A dermoscopy image of a single skin lesion:
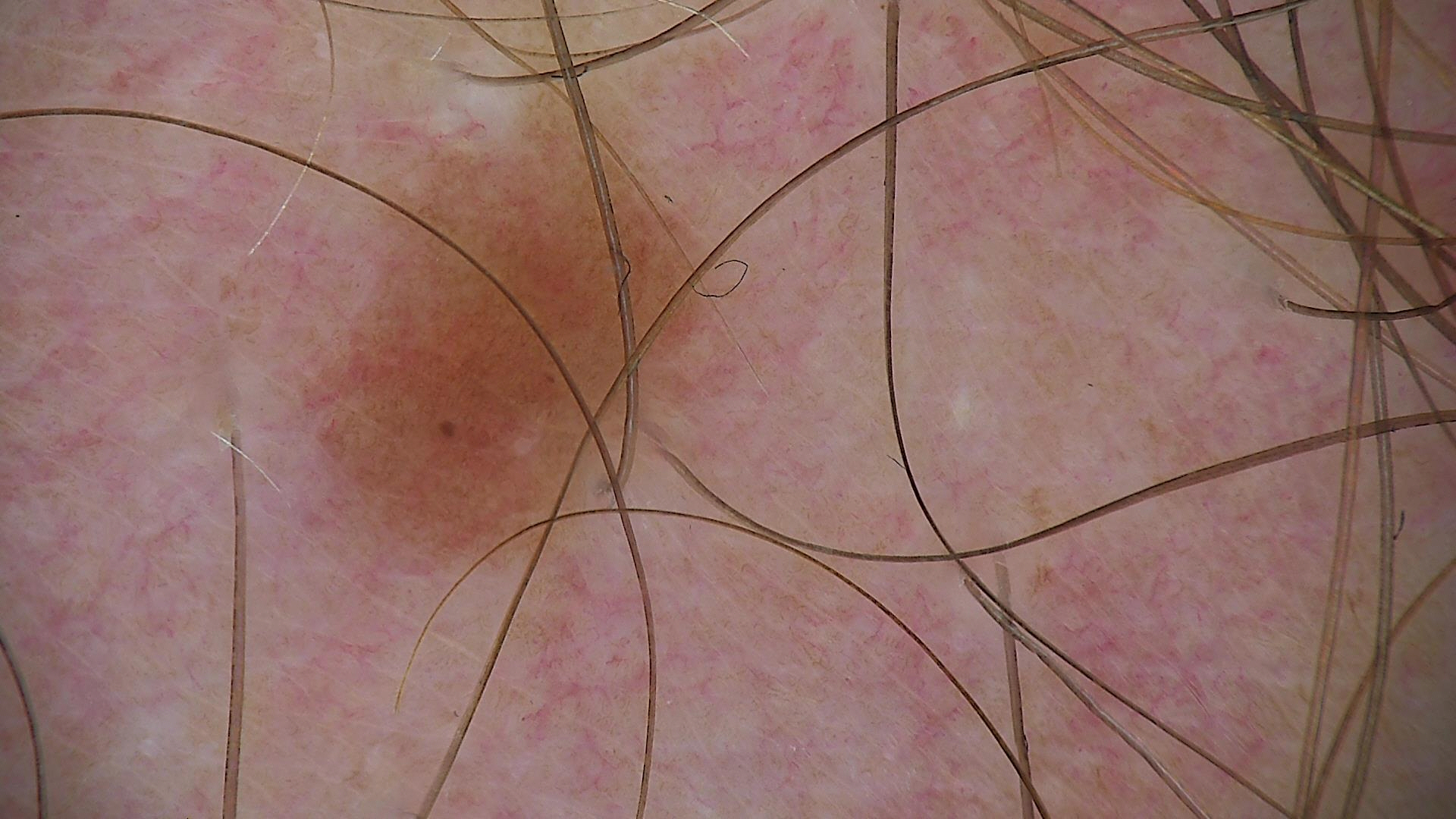The architecture is that of a banal lesion.
The diagnostic label was a junctional nevus.